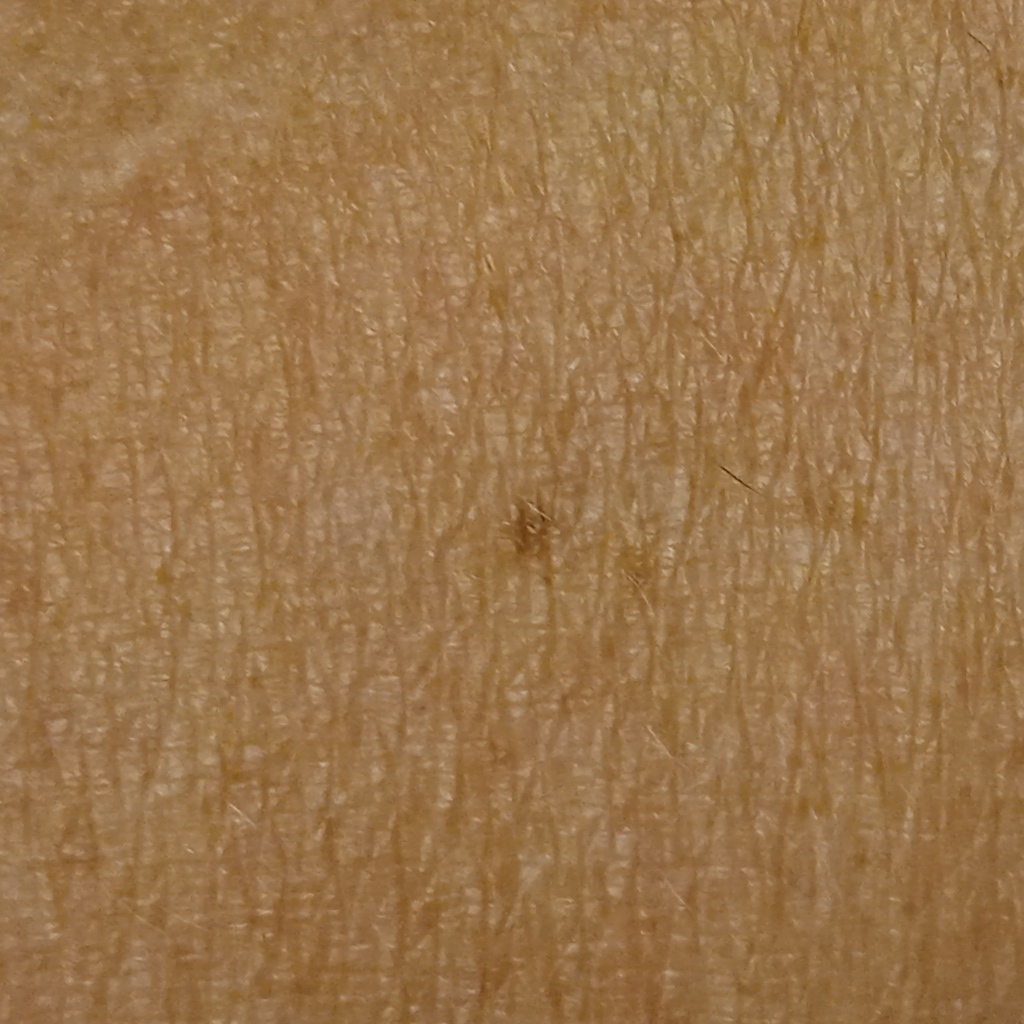The patient describes having a moderate number of moles.
The patient reports a personal history of cancer.
A male patient 54 years old.
The patient says their skin tans without first burning.
Acquired for a research image collection, with no referral diagnosis.
A clinical photograph showing a skin lesion.
Located on an arm.
The lesion is about 2.6 mm across.
The diagnostic impression was a melanocytic nevus.